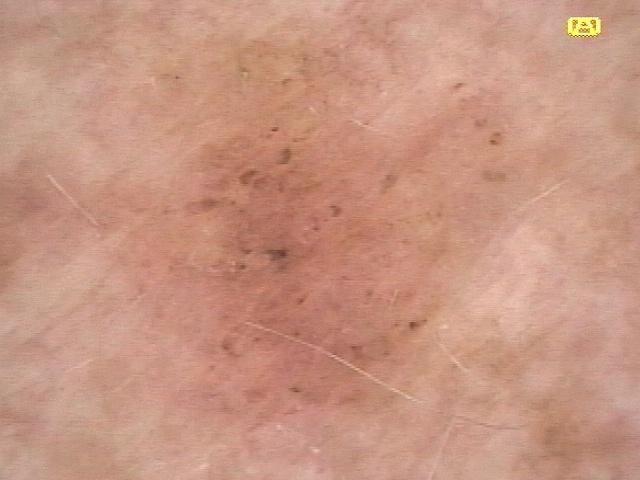subject: male, aged 58 to 62 | imaging: dermoscopic image | risk factors: a previous melanoma but no melanoma in first-degree relatives | skin phototype: II | site: the head or neck | diagnostic label: Seborrheic keratosis (clinical impression).